This is a close-up image; the lesion is described as fluid-filled and raised or bumpy; no constitutional symptoms were reported; the affected area is the leg.
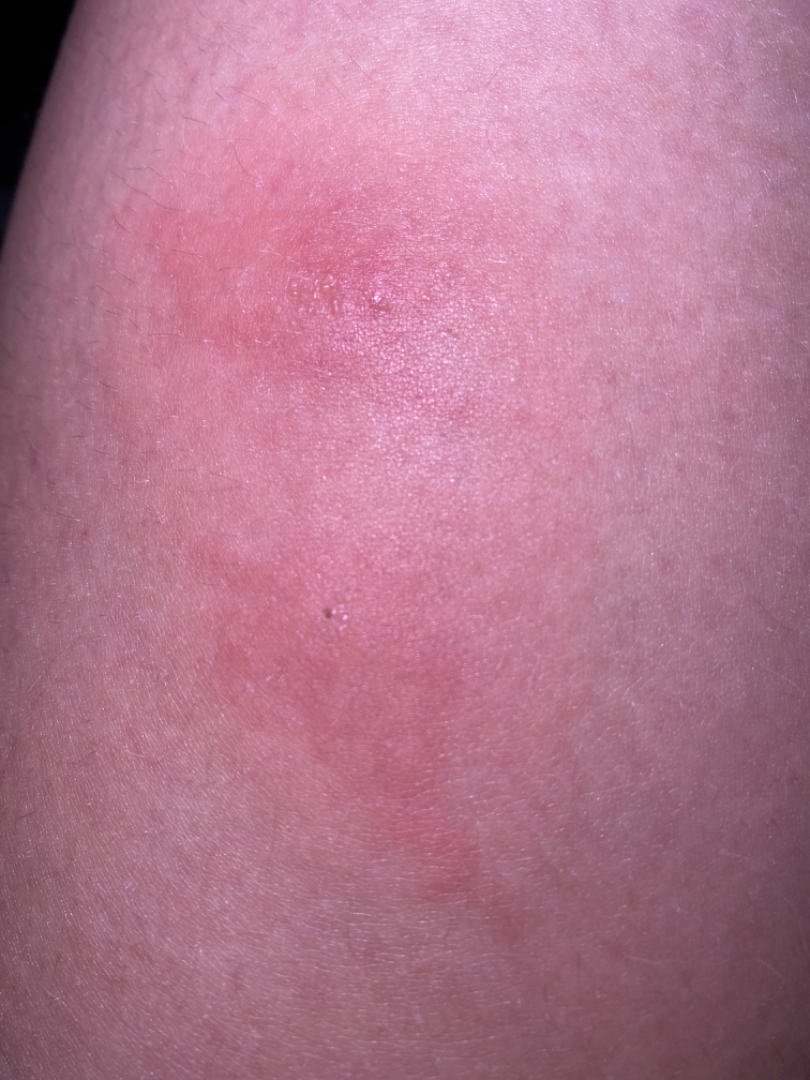Q: Could the case be diagnosed?
A: ungradable on photographic review